The subject is a male aged 33 to 37, a dermoscopic image of a skin lesion:
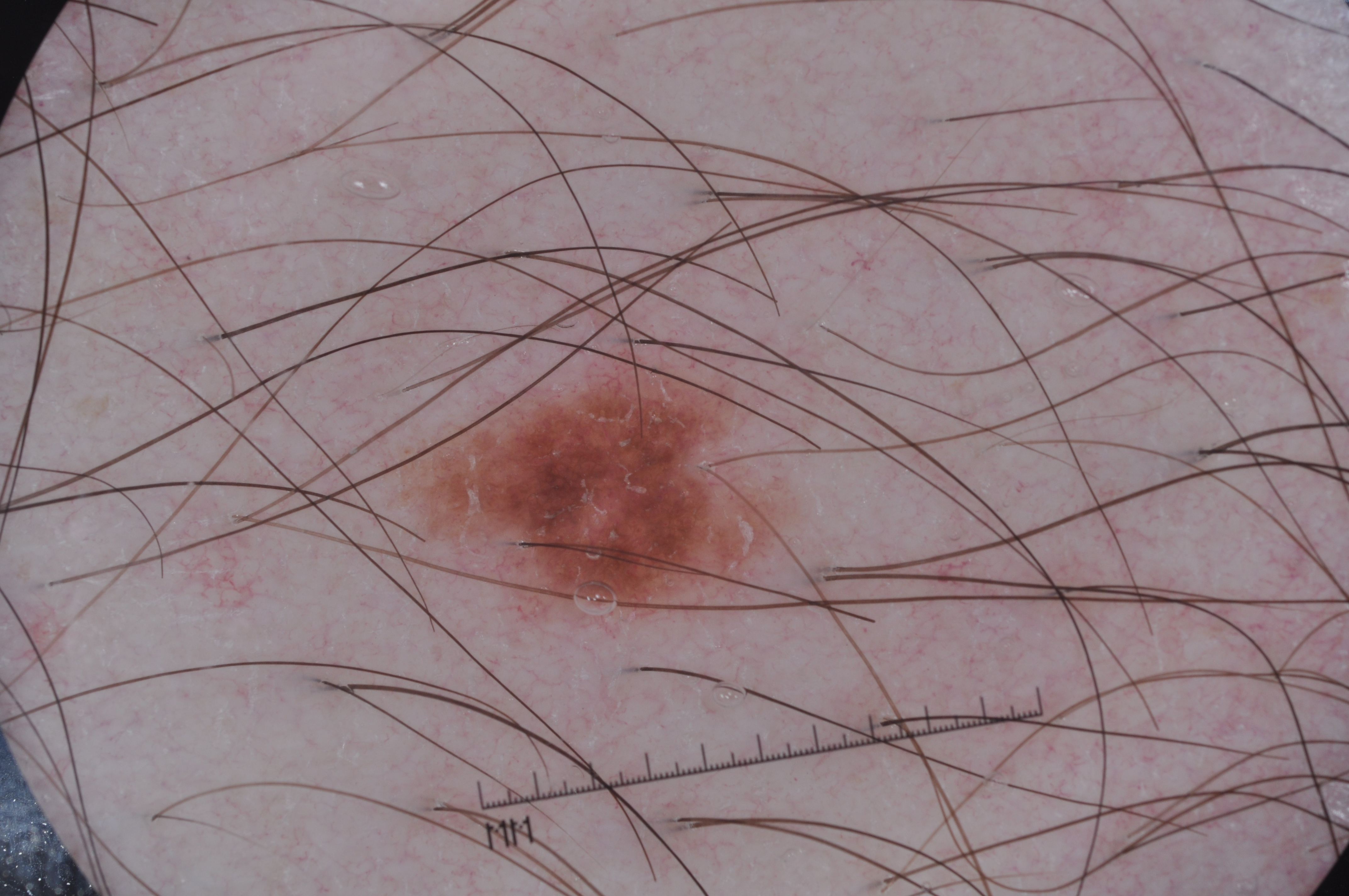{
  "lesion_location": {
    "bbox_xyxy": [
      422,
      357,
      769,
      616
    ]
  },
  "dermoscopic_features": {
    "present": [
      "pigment network"
    ],
    "absent": [
      "streaks",
      "negative network",
      "milia-like cysts"
    ]
  },
  "diagnosis": {
    "name": "melanocytic nevus",
    "malignancy": "benign",
    "lineage": "melanocytic",
    "provenance": "clinical"
  }
}